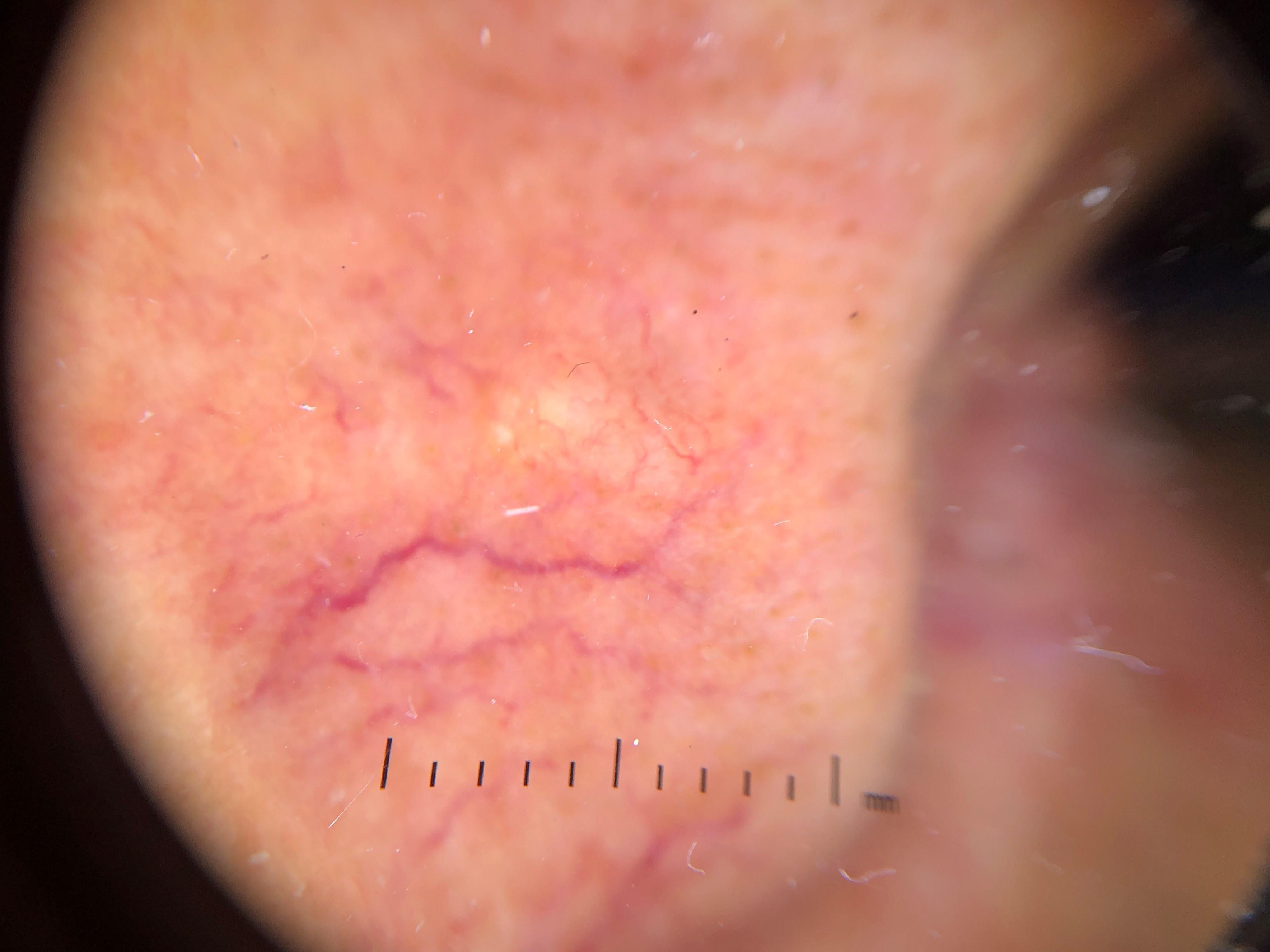imaging = contact-polarized dermoscopy
body site = the head or neck
pathology = Basal cell carcinoma (biopsy-proven)